Texture is reported as raised or bumpy; the lesion involves the front of the torso, arm and back of the torso; the condition has been present for one to three months; a close-up photograph; reported lesion symptoms include burning, pain and itching; associated systemic symptoms include chills.
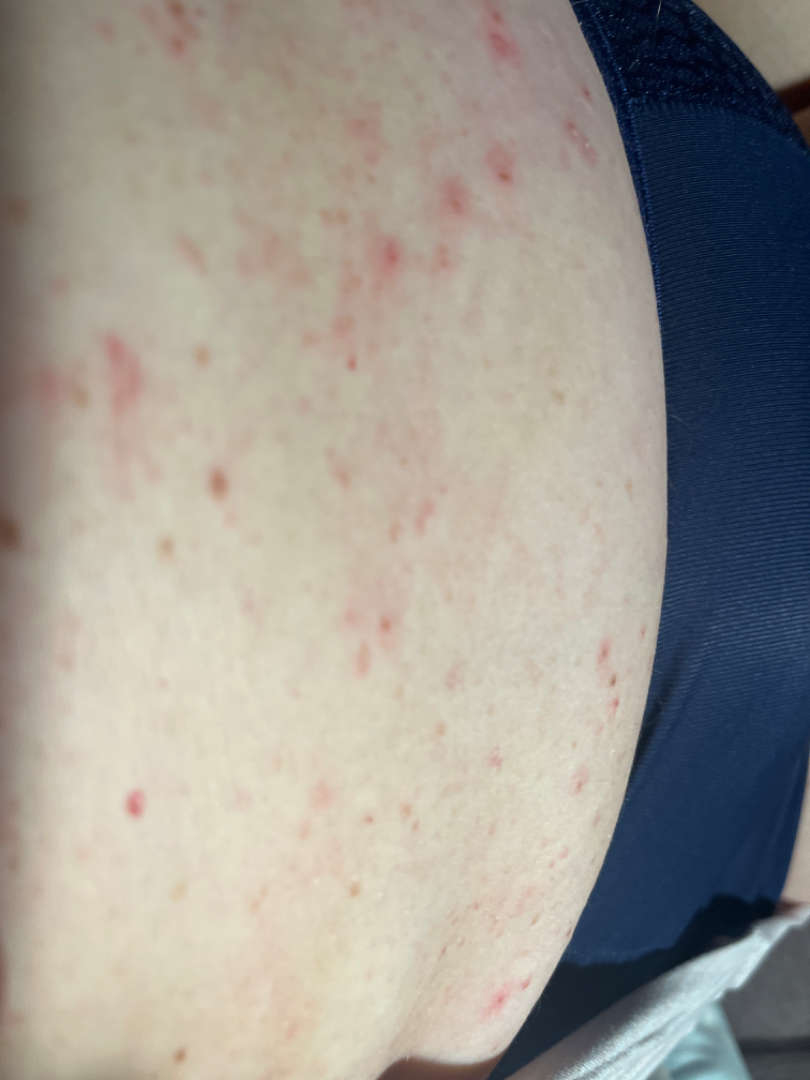The condition could not be reliably identified from the image.